The lesion involves the leg, reported lesion symptoms include bothersome appearance and itching, this image was taken at an angle, the lesion is described as raised or bumpy, present for less than one week, the patient is a male aged 30–39: 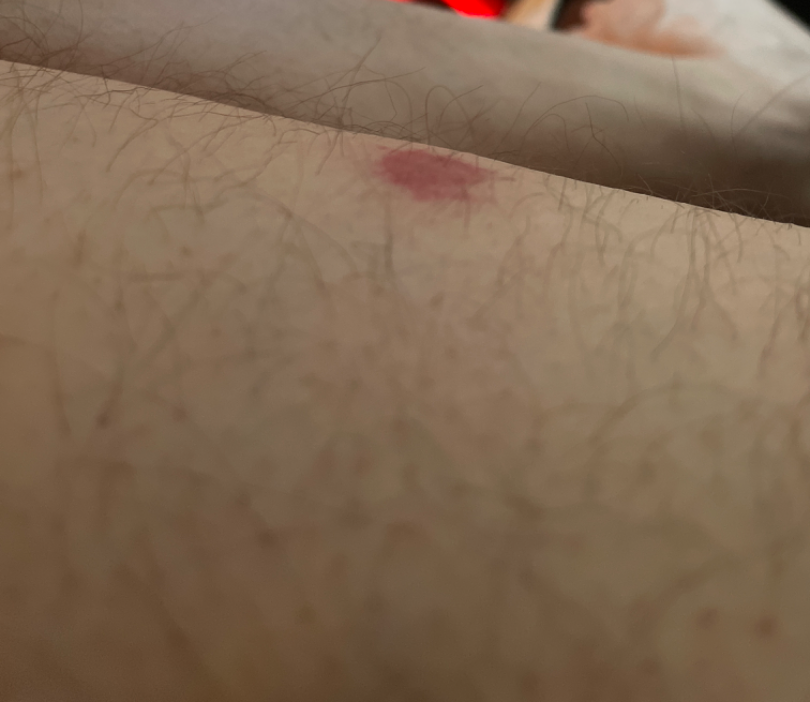On remote dermatologist review, the differential is split between Purpura and ecchymoses; less probable is Pigmented purpuric eruption; a remote consideration is Insect Bite; less likely is Hemangioma.